A dermoscopic close-up of a skin lesion: 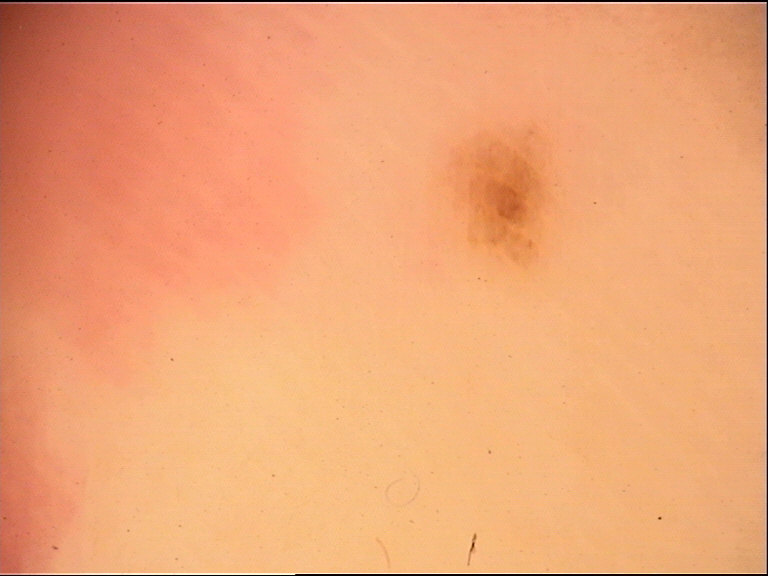lesion type = banal | assessment = acral junctional nevus (expert consensus).